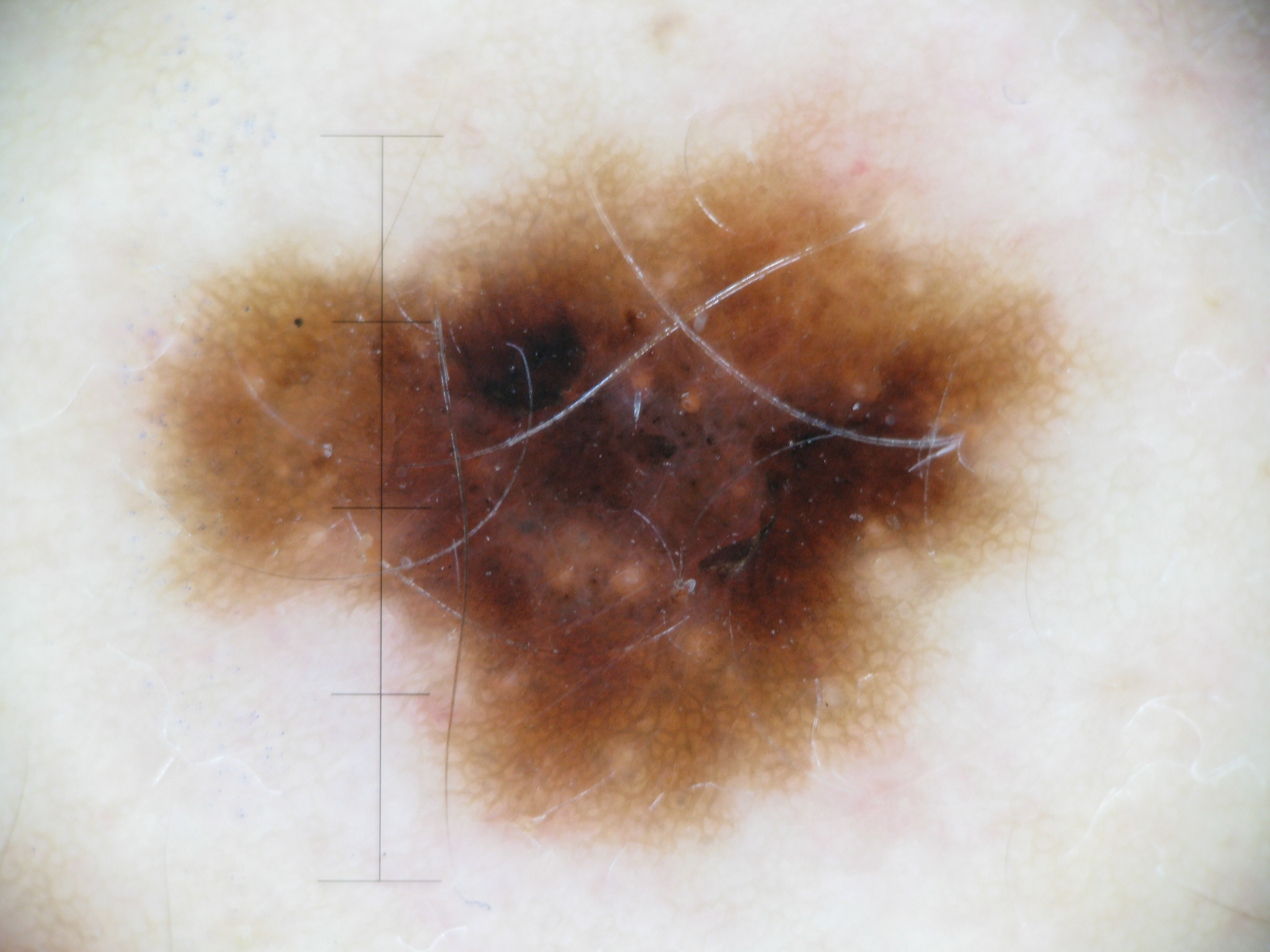Q: What was the diagnostic impression?
A: dysplastic compound nevus (expert consensus)